The lesion involves the leg, this image was taken at an angle.
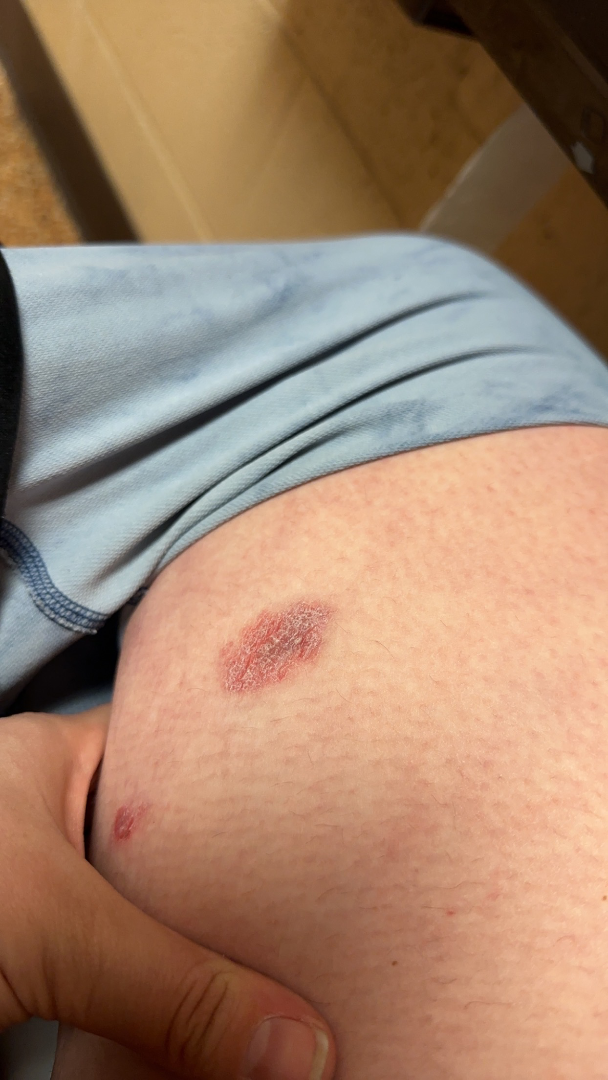Case summary:
– assessment: ungradable on photographic review